The photograph is a close-up of the affected area:
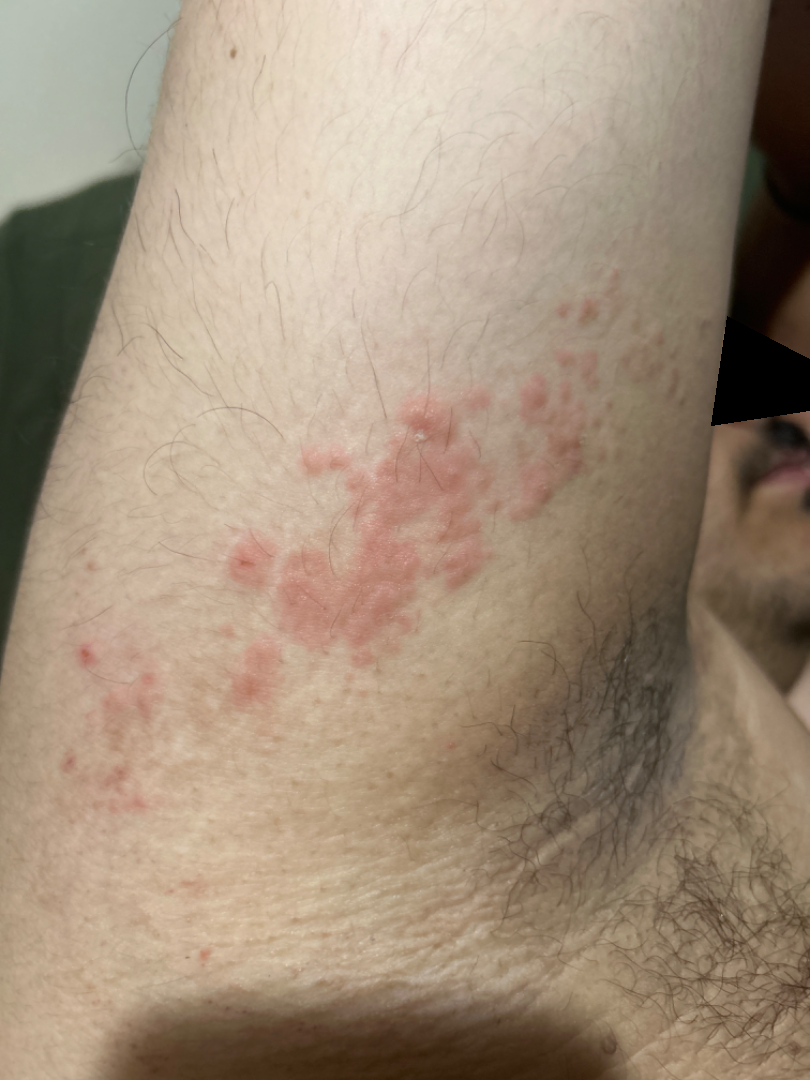The favored diagnosis is Allergic Contact Dermatitis; also on the differential is Eczema.